A patient in their mid-80s · a clinical photograph of a skin lesion:
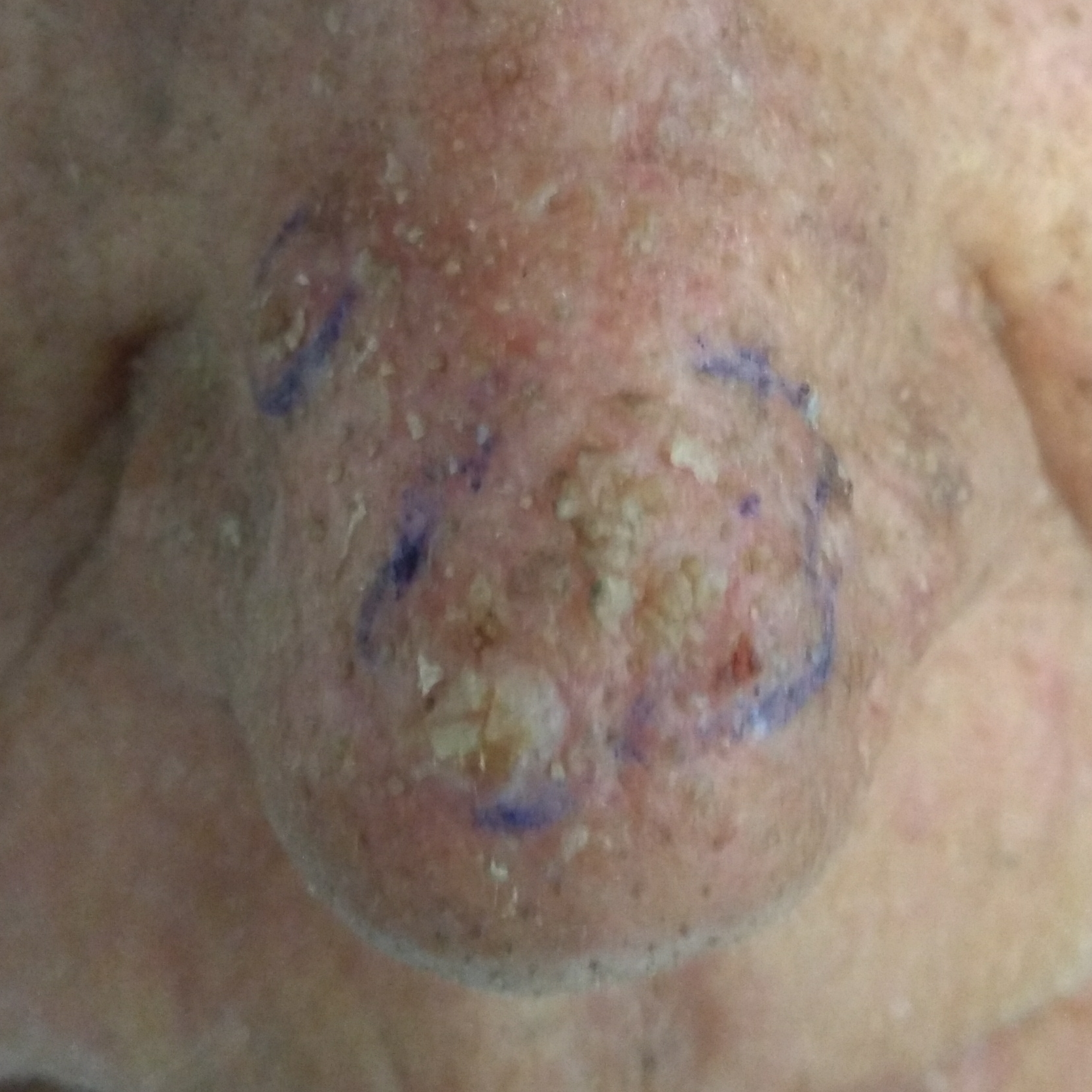Located on the nose. The patient describes that the lesion has grown, is elevated, and itches, but has not changed. Consistent with an actinic keratosis.